The patient is a female aged 50–59. The head or neck is involved. The photo was captured at a distance:
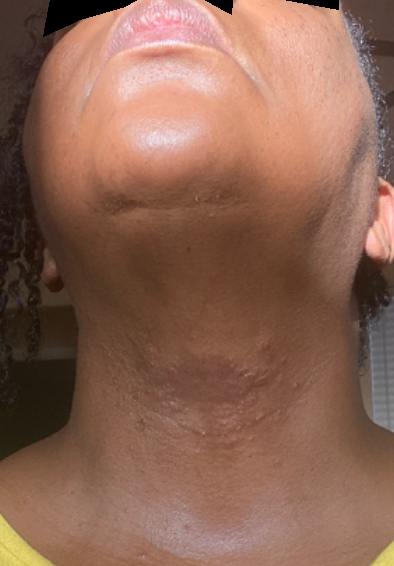The reviewing dermatologists' impression was: Allergic Contact Dermatitis and Cutaneous sarcoidosis were considered with similar weight; less probable is Eczema; a more distant consideration is Drug Rash; lower on the differential is Lichenoid myxedema.